A close-up photograph: 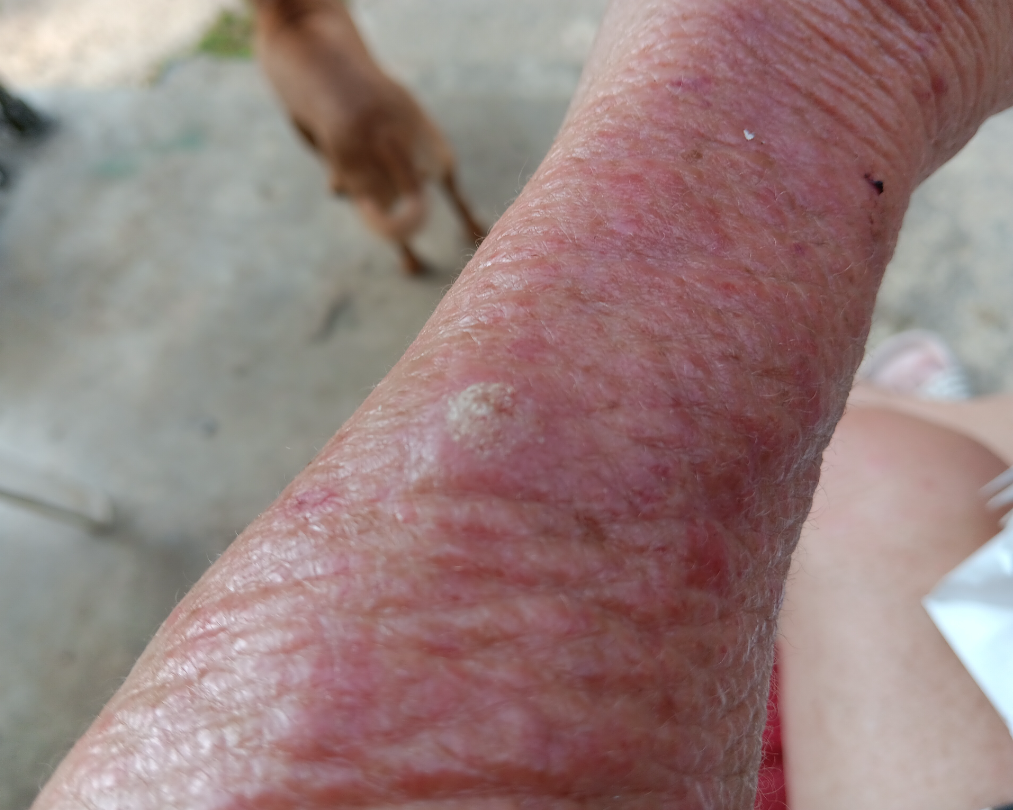<case>
  <texture>rough or flaky</texture>
  <skin_tone>
    <fitzpatrick>I</fitzpatrick>
  </skin_tone>
  <differential>SCC/SCCIS</differential>
</case>